A skin lesion imaged with a dermatoscope:
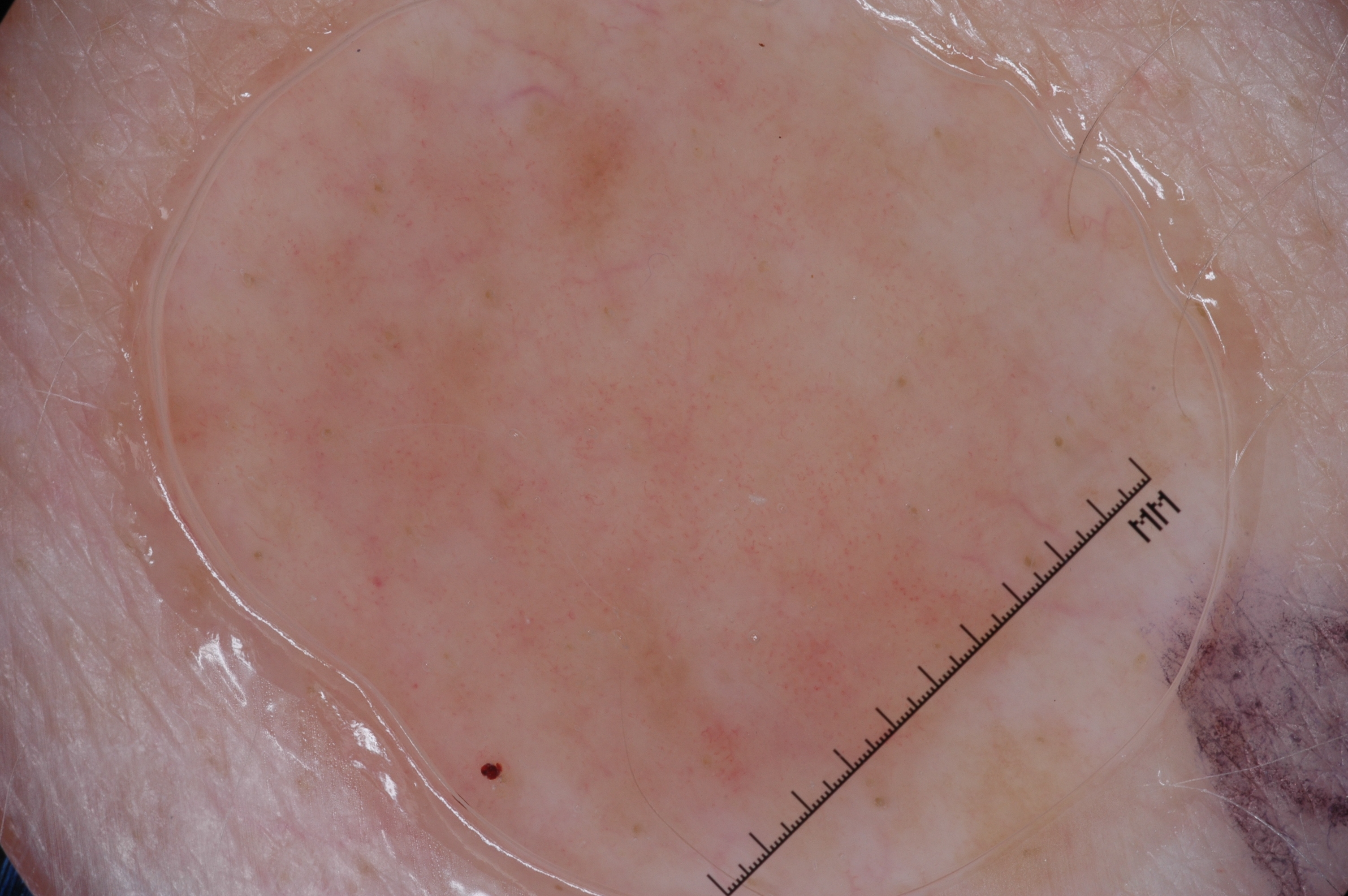Q: Where is the lesion located?
A: 218 74 1078 851
Q: Which dermoscopic features were noted?
A: milia-like cysts
Q: How much of the field does the lesion occupy?
A: ~41% of the field
Q: What did the assessment conclude?
A: a seborrheic keratosis, a benign skin lesion